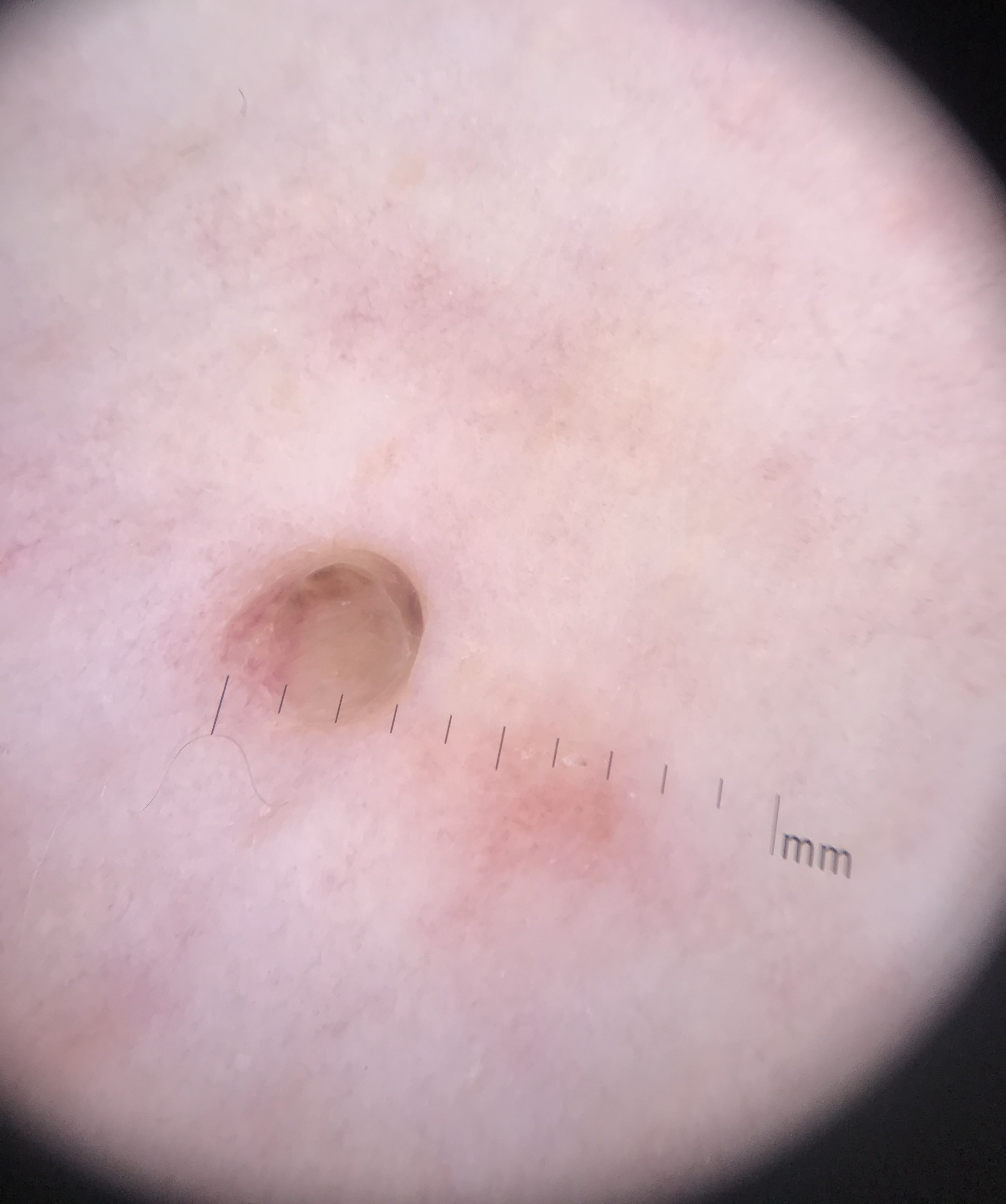image type = dermoscopy
classification = banal
label = dermal nevus (expert consensus)